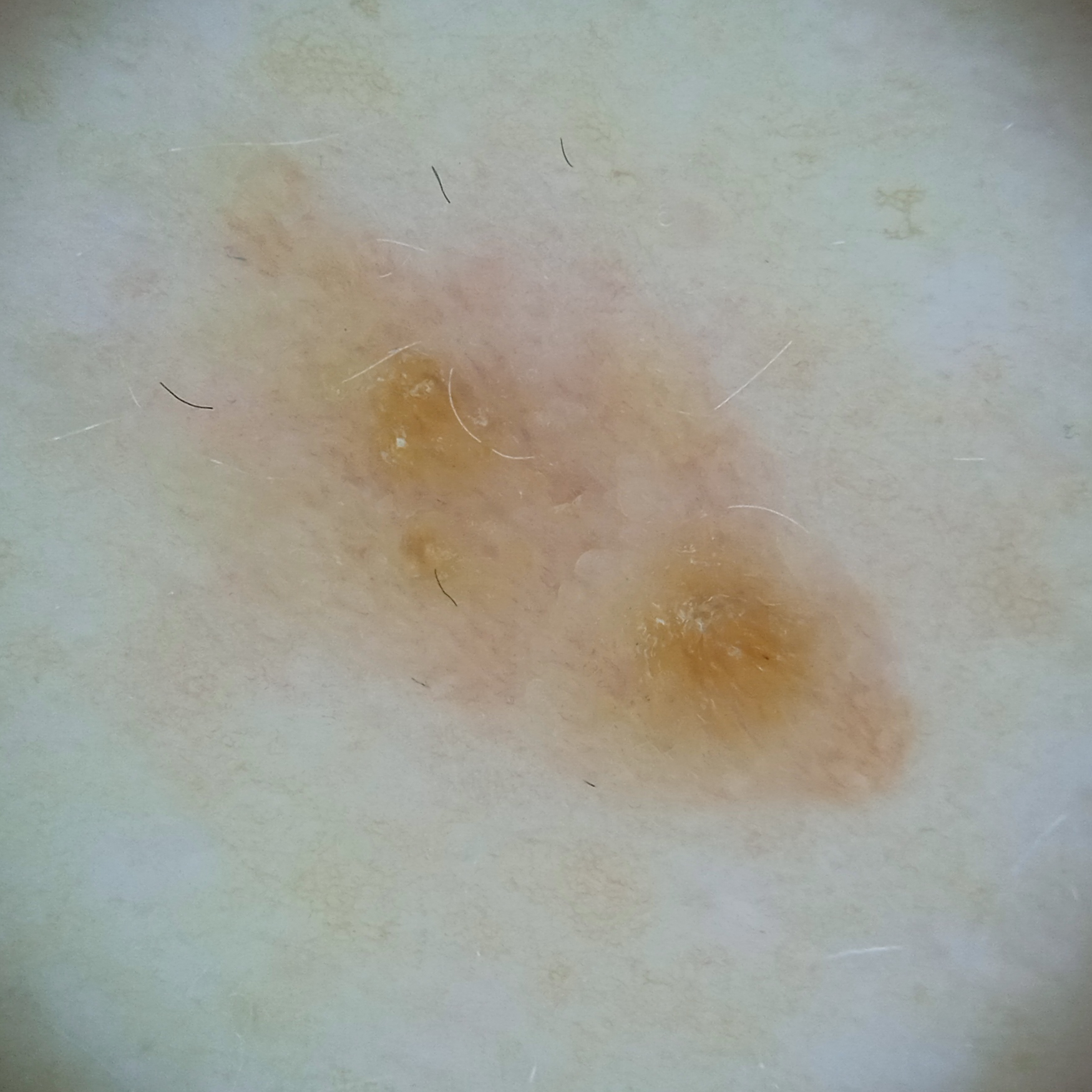Q: What is the patient's nevus burden?
A: a moderate number of melanocytic nevi
Q: Why was this imaged?
A: research study (no referral diagnosis)
Q: What kind of image is this?
A: dermoscopic image
Q: Patient demographics?
A: female, 59 years old
Q: How does the patient's skin react to sun?
A: skin reddens with sun exposure
Q: Where is the lesion?
A: the torso
Q: What was the diagnosis?
A: seborrheic keratosis (dermatologist consensus)